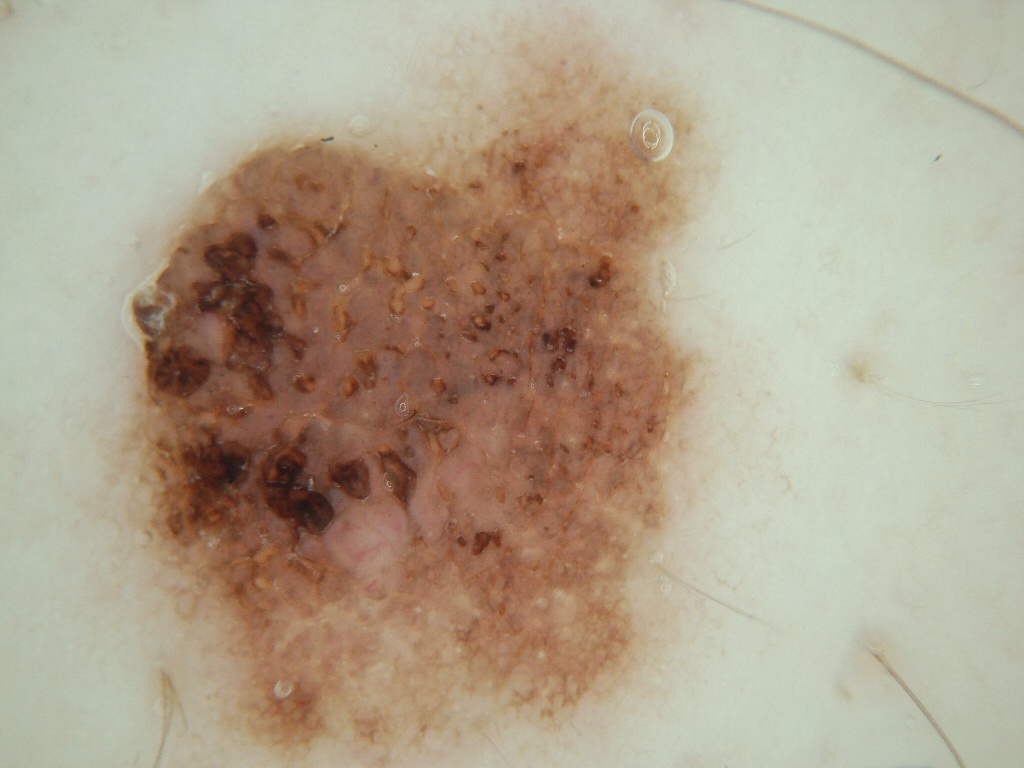A dermoscopic image of a skin lesion.
The lesion is bounded by left=67, top=3, right=758, bottom=764.
Expert review diagnosed this as a benign skin lesion.